The patient considered this a rash · reported duration is one to four weeks · skin tone: Fitzpatrick phototype III; human graders estimated Monk skin tone scale 3 or 4 (two reviewer pools) · the patient indicates the lesion is raised or bumpy · located on the arm · male patient, age 30–39 · symptoms reported: enlargement, bothersome appearance and itching · this image was taken at a distance: 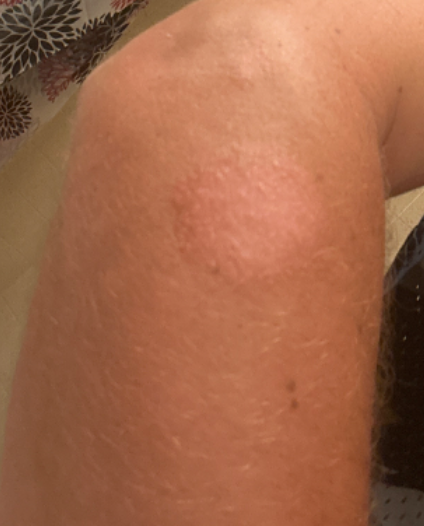Assessment:
Tinea (leading); Eczema (possible); Erythema annulare centrifugum (remote).